A dermoscopic photograph of a skin lesion: 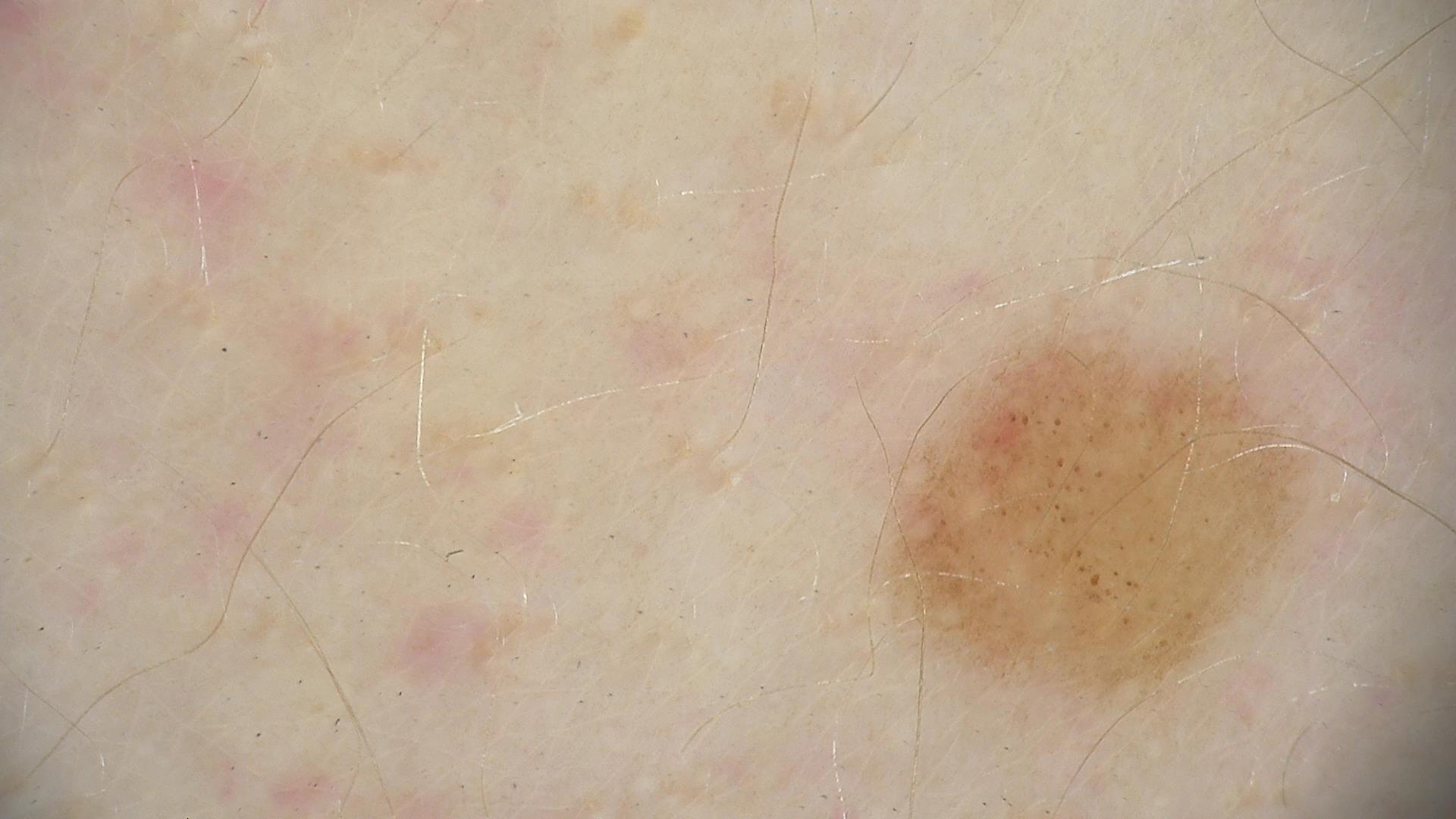Impression:
The diagnosis was a benign lesion — a dysplastic junctional nevus.